This image was taken at an angle, located on the arm:
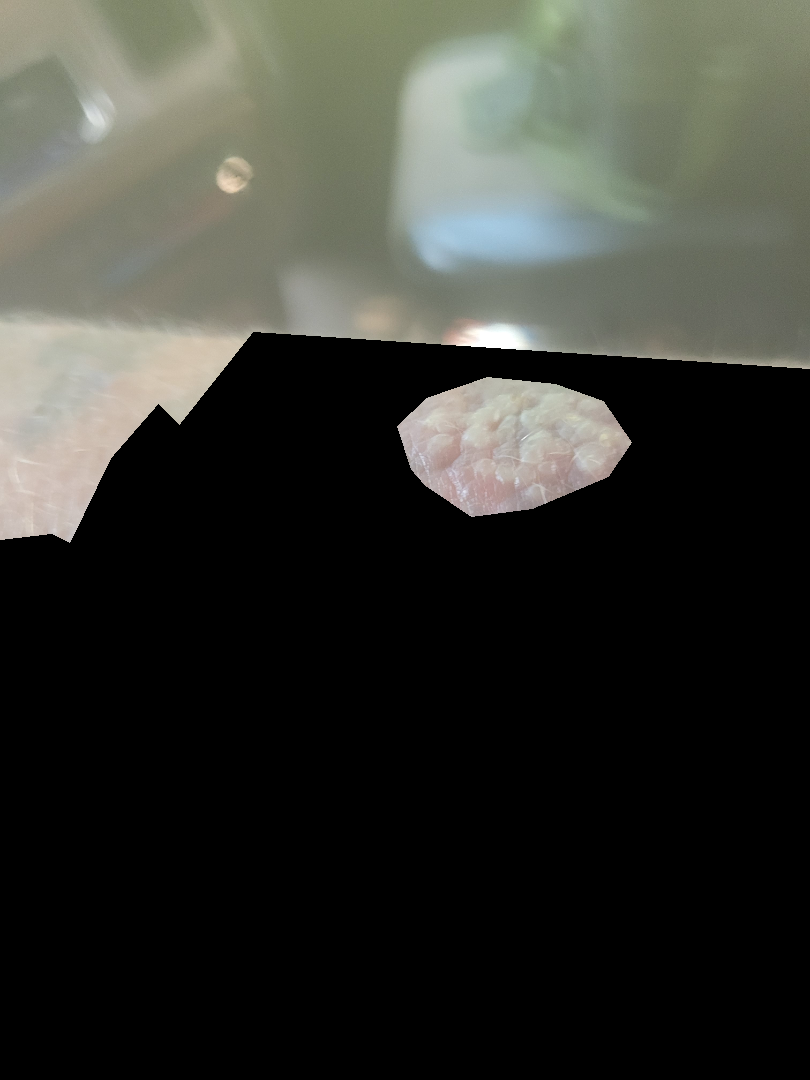Q: Could the case be diagnosed?
A: ungradable on photographic review
Q: Texture?
A: fluid-filled and raised or bumpy
Q: Reported symptoms?
A: burning, itching, bothersome appearance and pain
Q: How long has this been present?
A: less than one week